This is a dermoscopic photograph of a skin lesion:
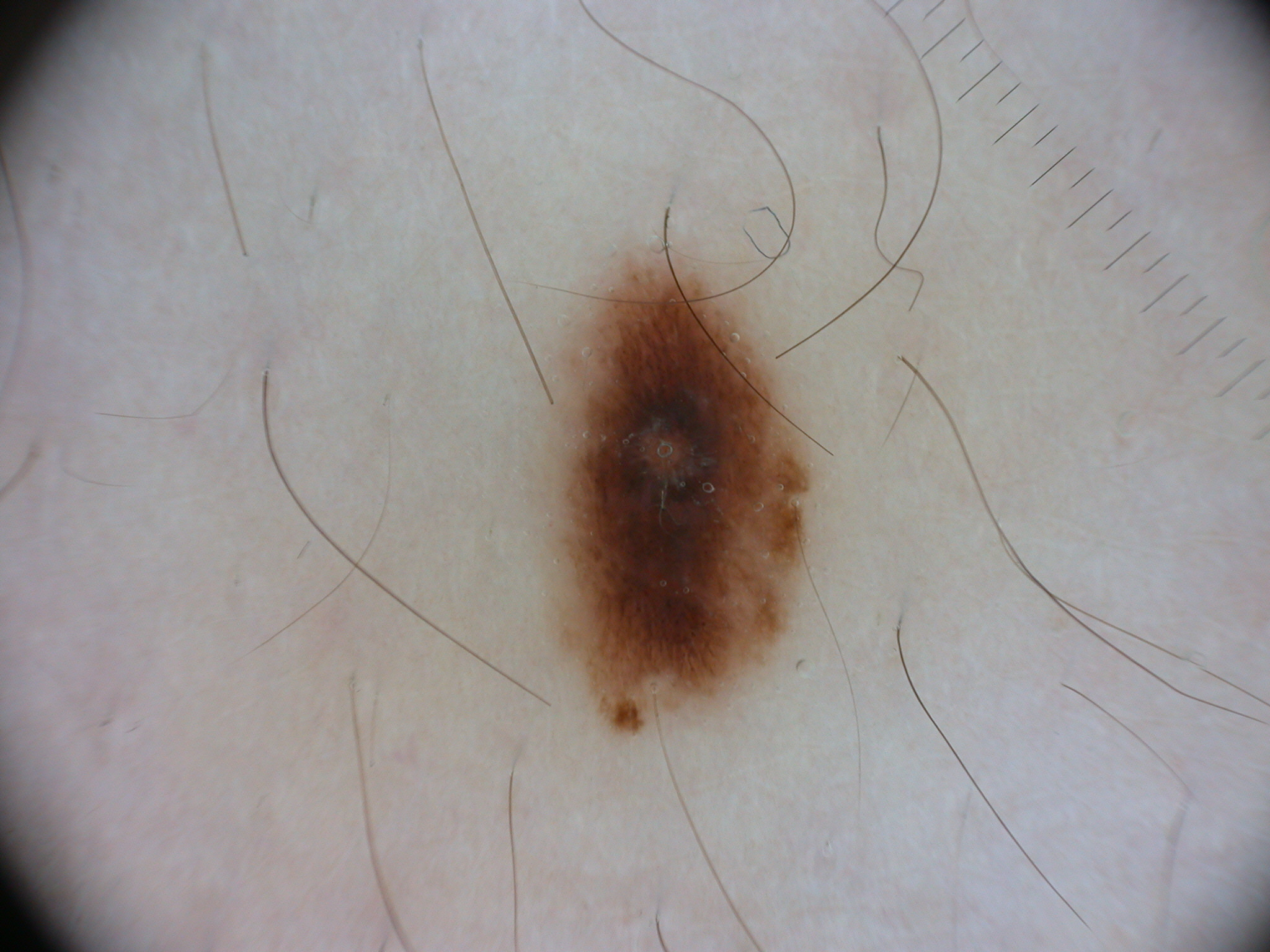The lesion is bounded by 534, 242, 815, 741. The dermoscopic pattern shows pigment network. The lesion takes up a moderate portion of the field. The lesion was assessed as a melanocytic nevus, a benign lesion.